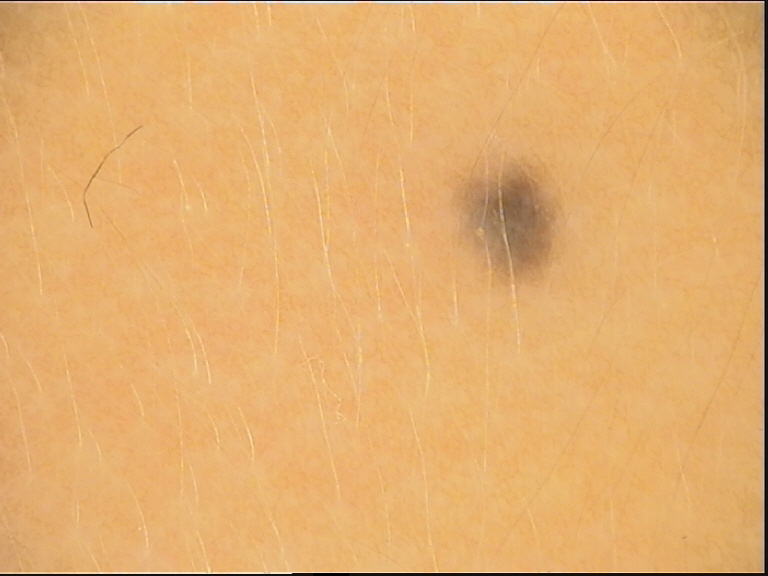* assessment: blue nevus (expert consensus)